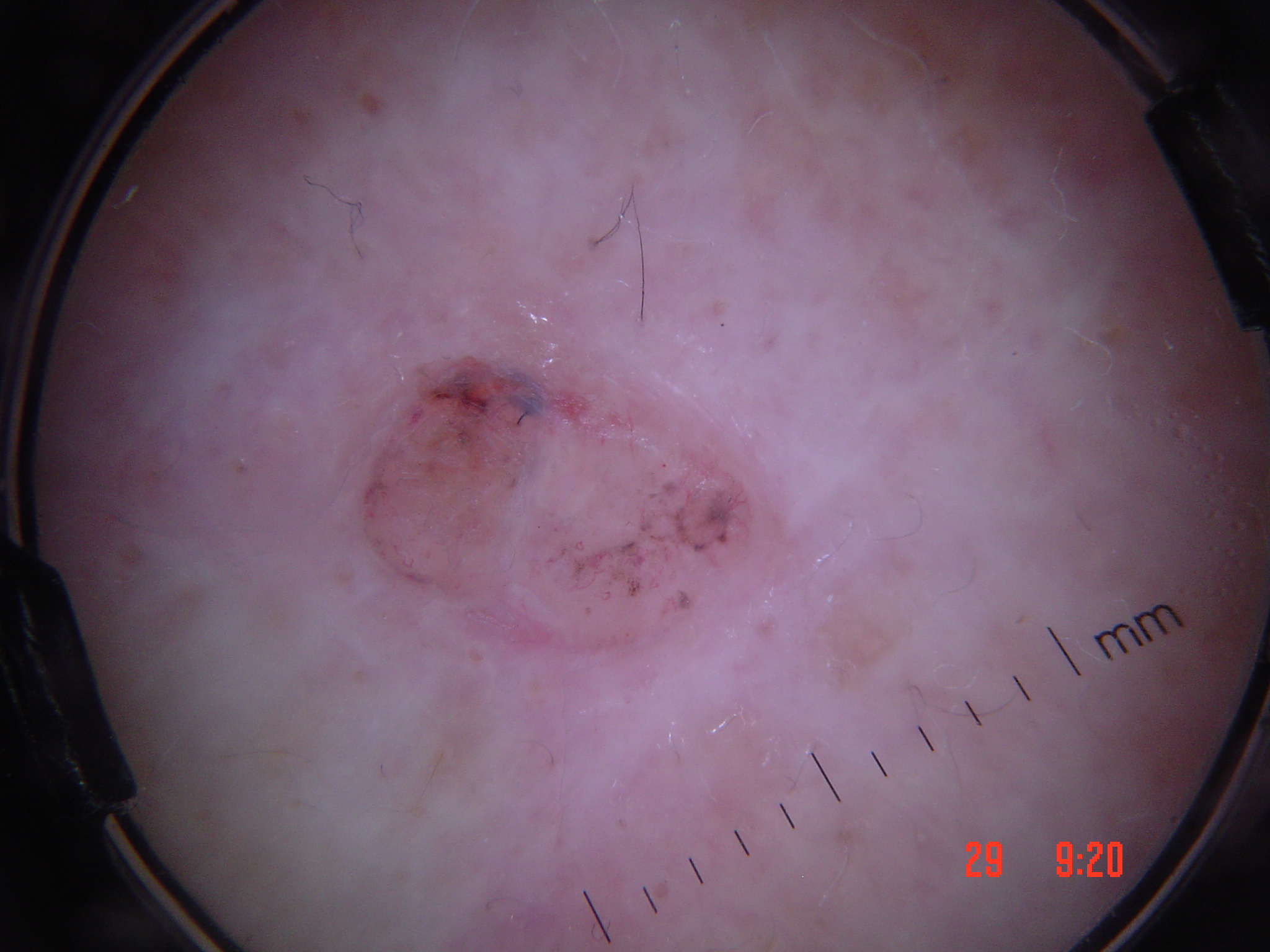Q: What is the diagnosis?
A: basal cell carcinoma (biopsy-proven)